A skin lesion imaged with a dermatoscope.
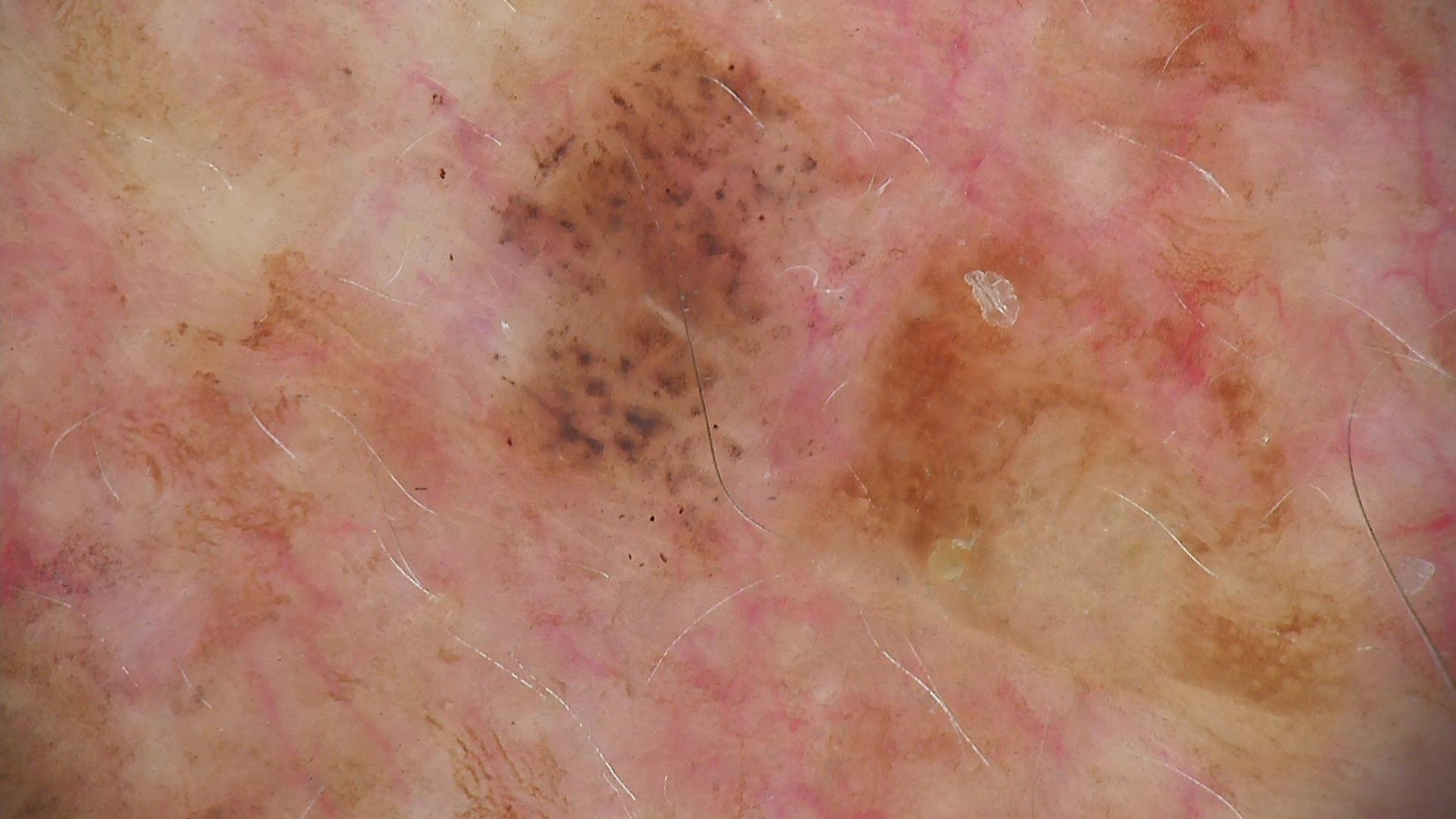Labeled as a keratinocytic lesion — a seborrheic keratosis.